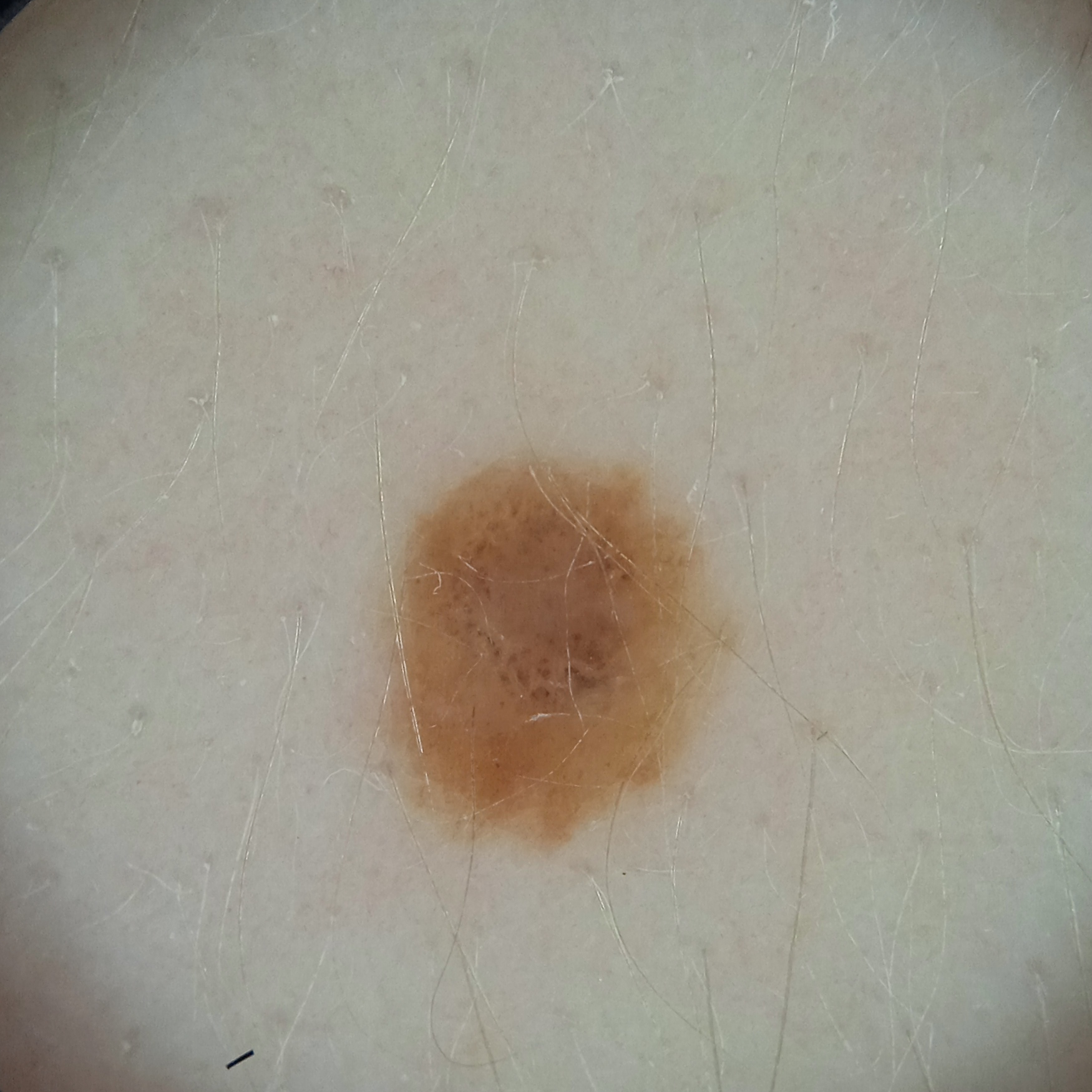diagnosis = melanocytic nevus (dermatologist consensus)